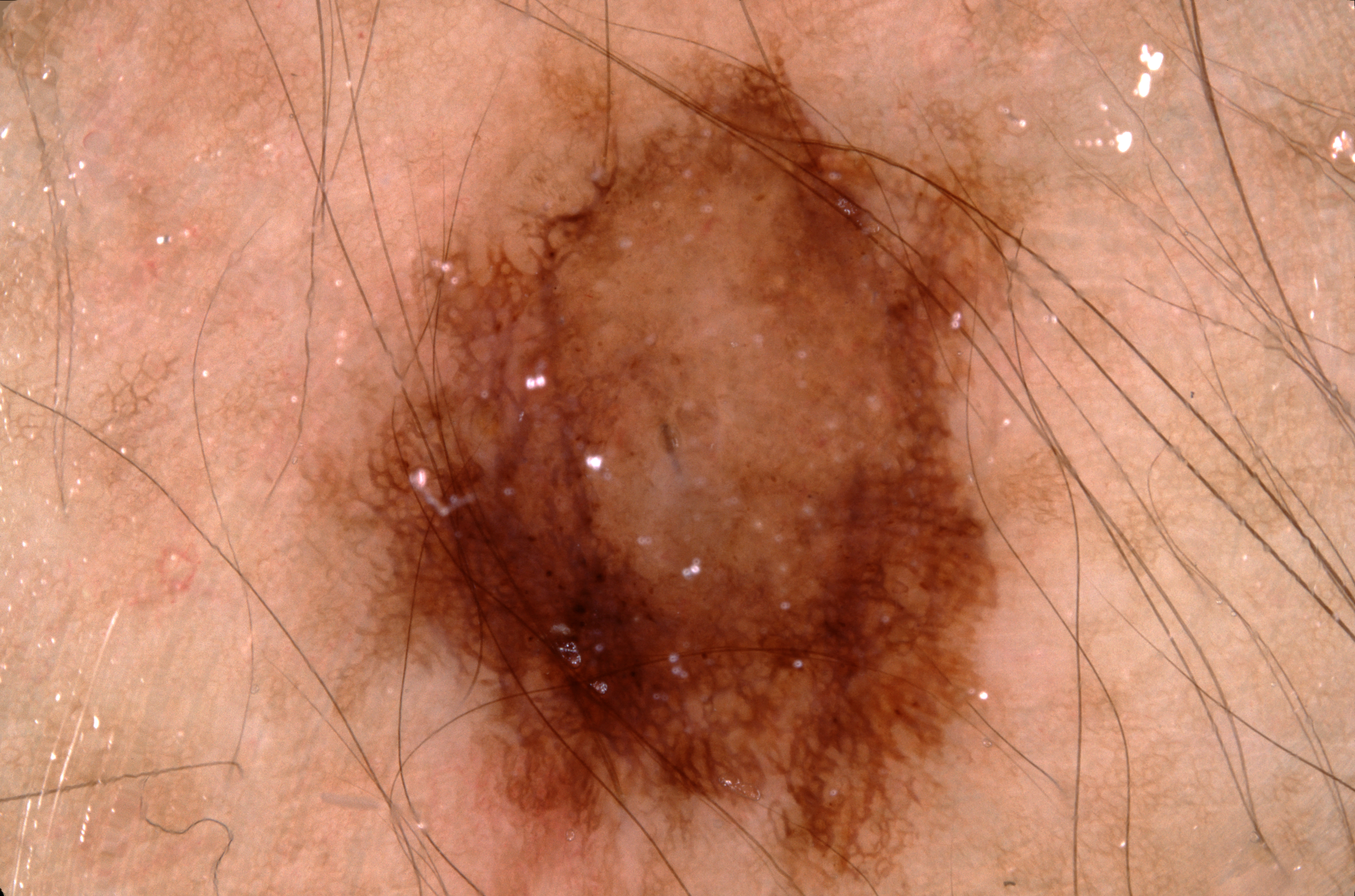A male patient aged around 50. This is a dermoscopic photograph of a skin lesion. The lesion's extent is [304, 0, 1058, 895]. Dermoscopy demonstrates pigment network. The diagnostic assessment was a melanocytic nevus.